This is a close-up image. Female subject, age 30–39. Located on the leg.
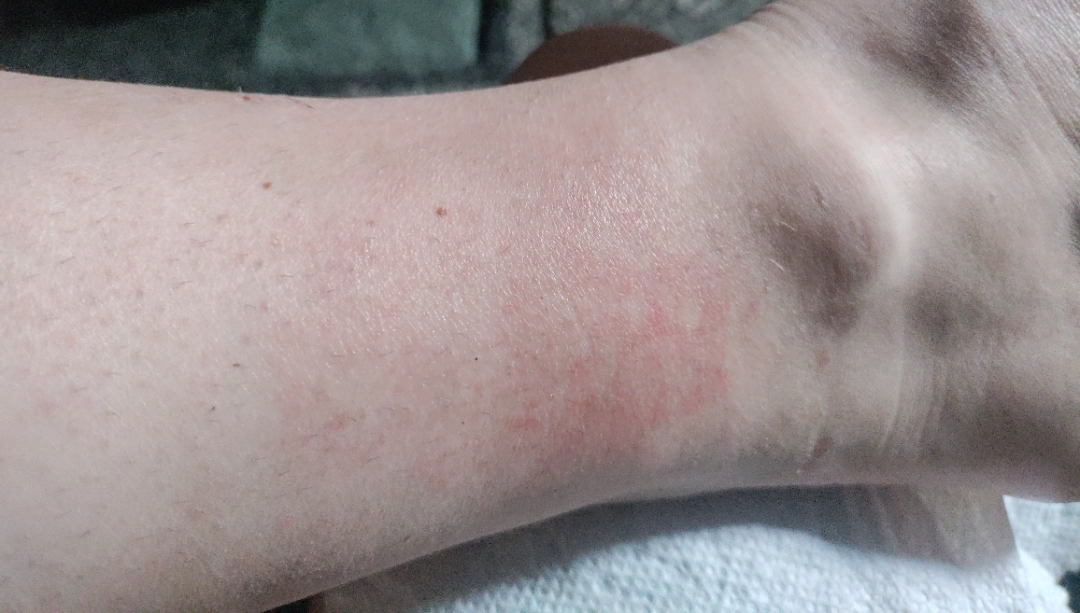Findings:
One reviewing dermatologist: Stasis Dermatitis; Acute dermatitis, NOS; and Allergic Contact Dermatitis were considered with similar weight.